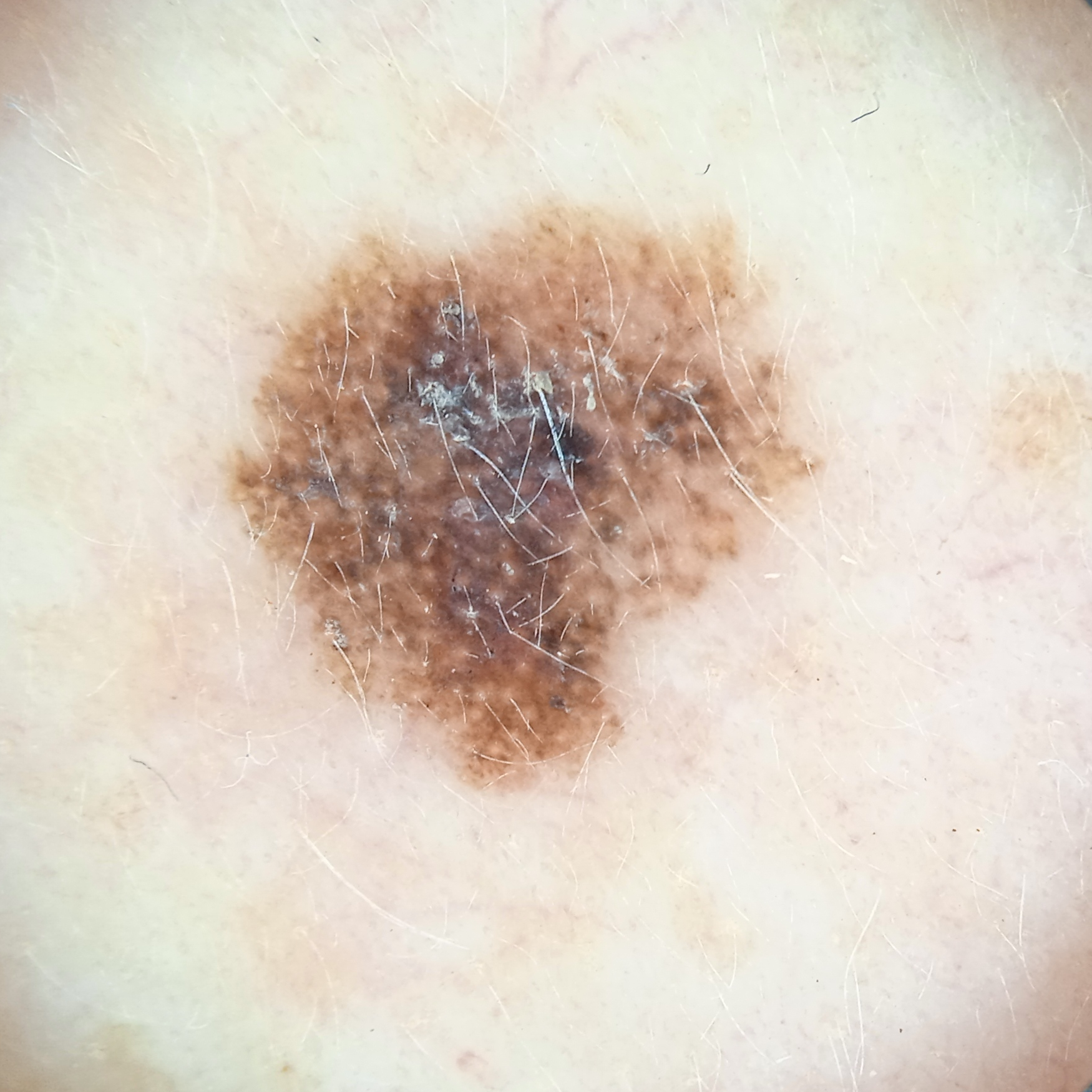sun reaction — skin reddens with sun exposure; image type — dermoscopy; nevus count — a moderate number of melanocytic nevi; risk factors — a personal history of skin cancer; referral — clinical suspicion of melanoma; patient — female, age 50; location — the face; diagnosis — melanoma (biopsy-proven).